A male subject, aged 13-17; a dermoscopic view of a skin lesion: 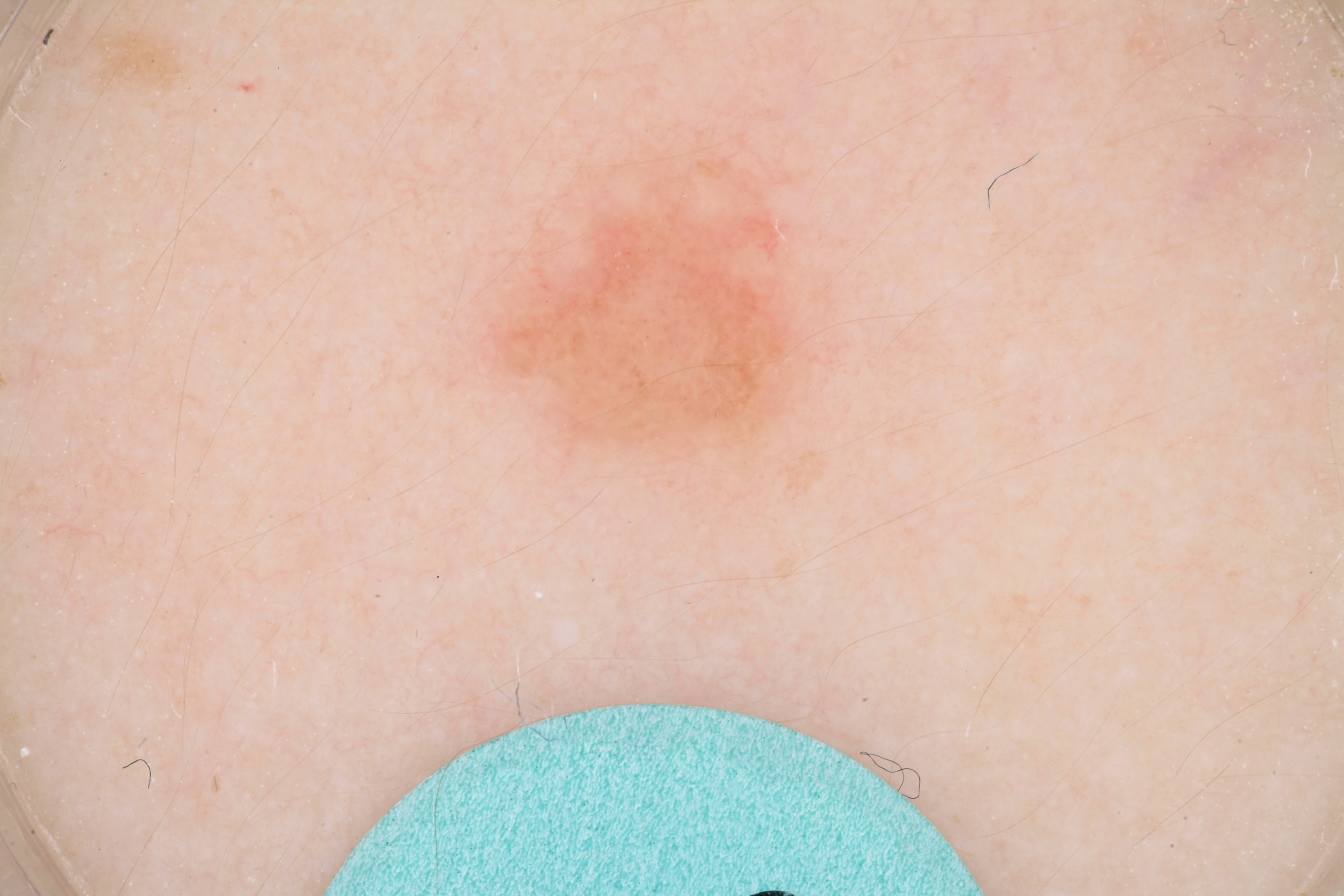Image and clinical context: A mid-sized lesion within the field. Lesion location: bbox(471, 137, 834, 465). The dermoscopic pattern shows milia-like cysts. Conclusion: Consistent with a melanocytic nevus, a benign lesion.